The patient is a female about 40 years old, a dermoscopic close-up of a skin lesion.
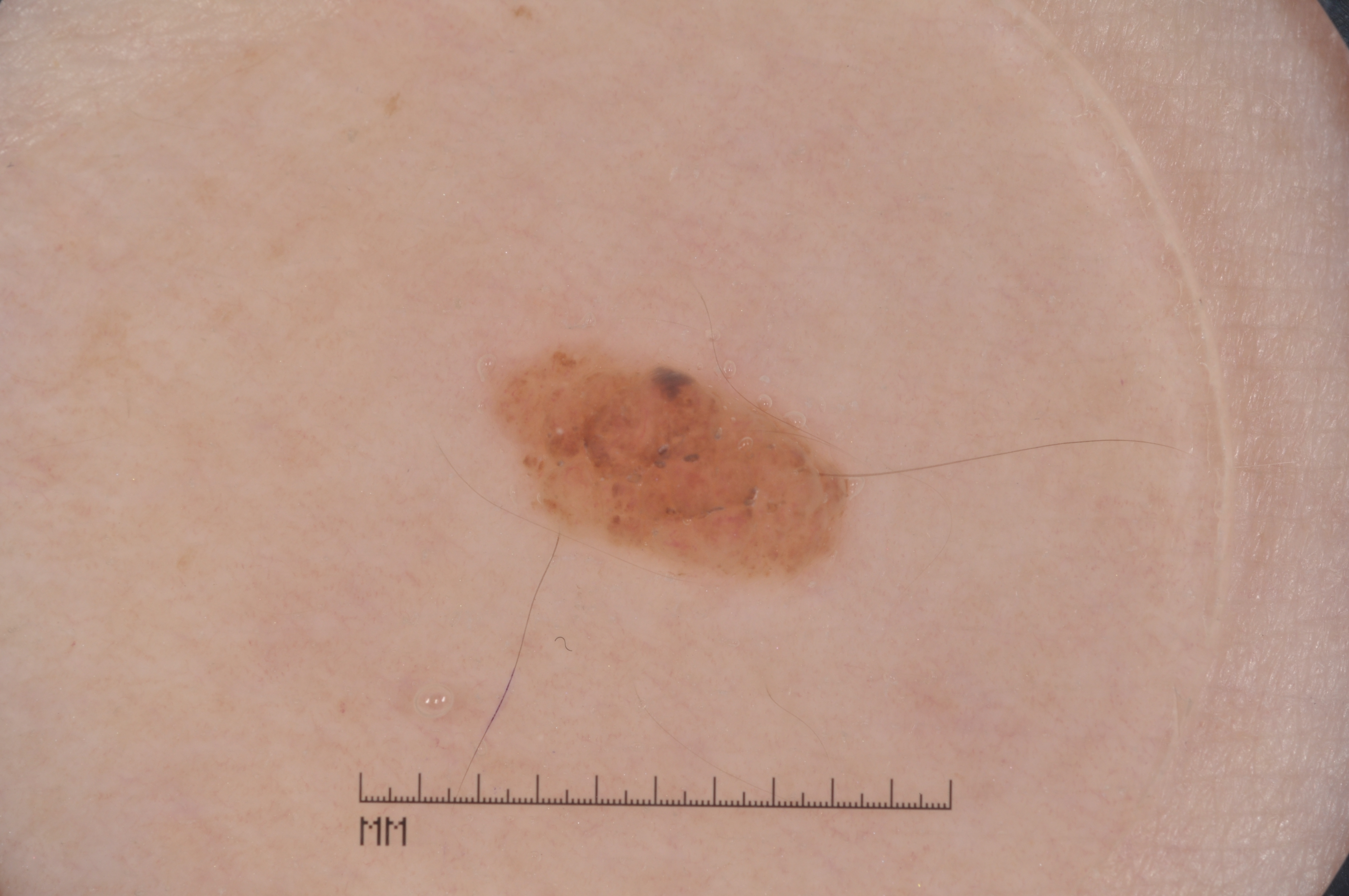Summary: As (left, top, right, bottom), the lesion is located at <box>495, 343, 843, 581</box>. Dermoscopic assessment notes milia-like cysts, with no negative network, streaks, or pigment network. Impression: The diagnostic assessment was a melanocytic nevus, a benign lesion.